Dermoscopy of a skin lesion: 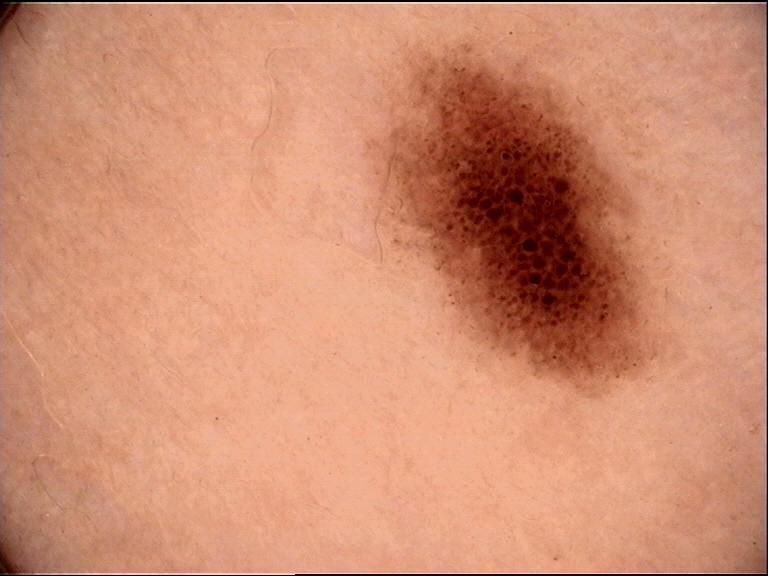Q: What is the diagnosis?
A: dysplastic junctional nevus (expert consensus)